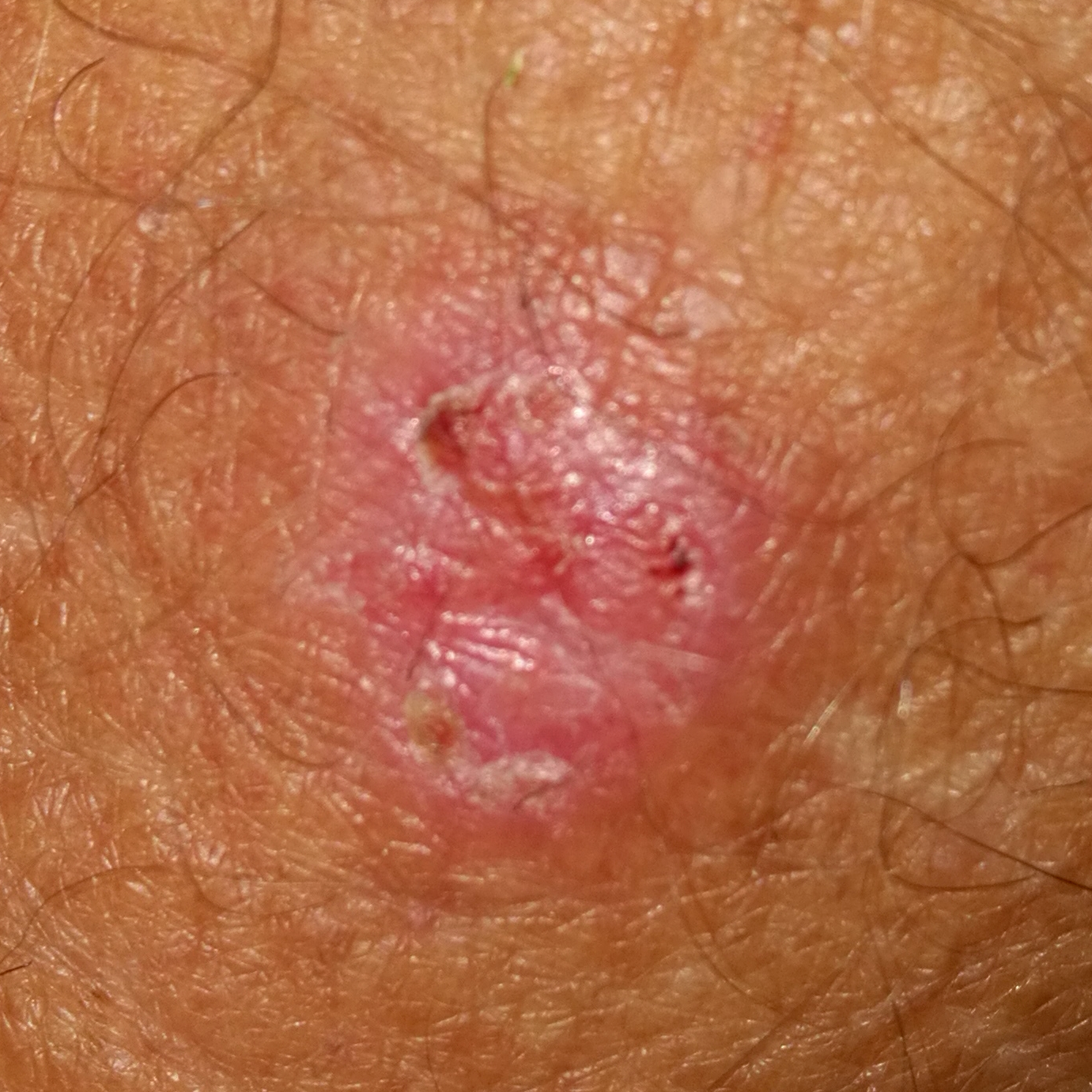Summary:
A male patient age 62. A clinical photograph of a skin lesion. The lesion is located on an arm. Per patient report, the lesion has grown, has bled, hurts, itches, and is elevated.
Diagnosis:
Confirmed on histopathology as a basal cell carcinoma.